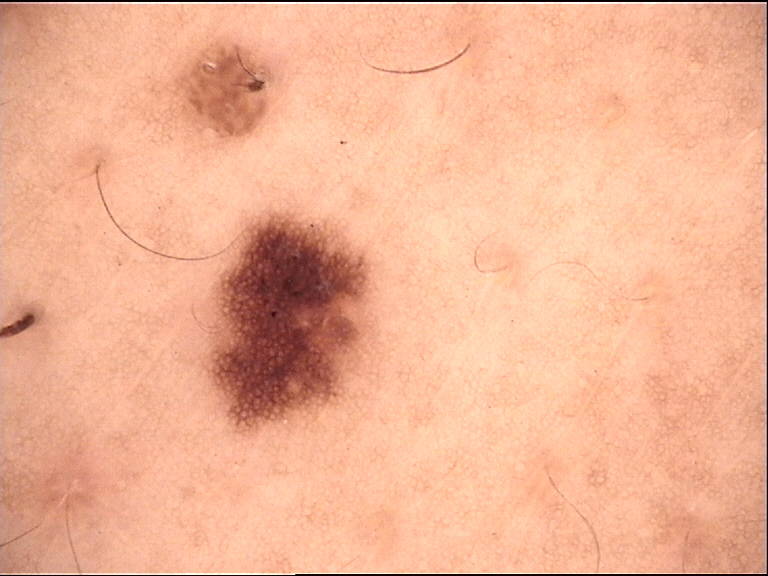| feature | finding |
|---|---|
| imaging | dermoscopy |
| label | junctional nevus (expert consensus) |